This is a dermoscopic photograph of a skin lesion — 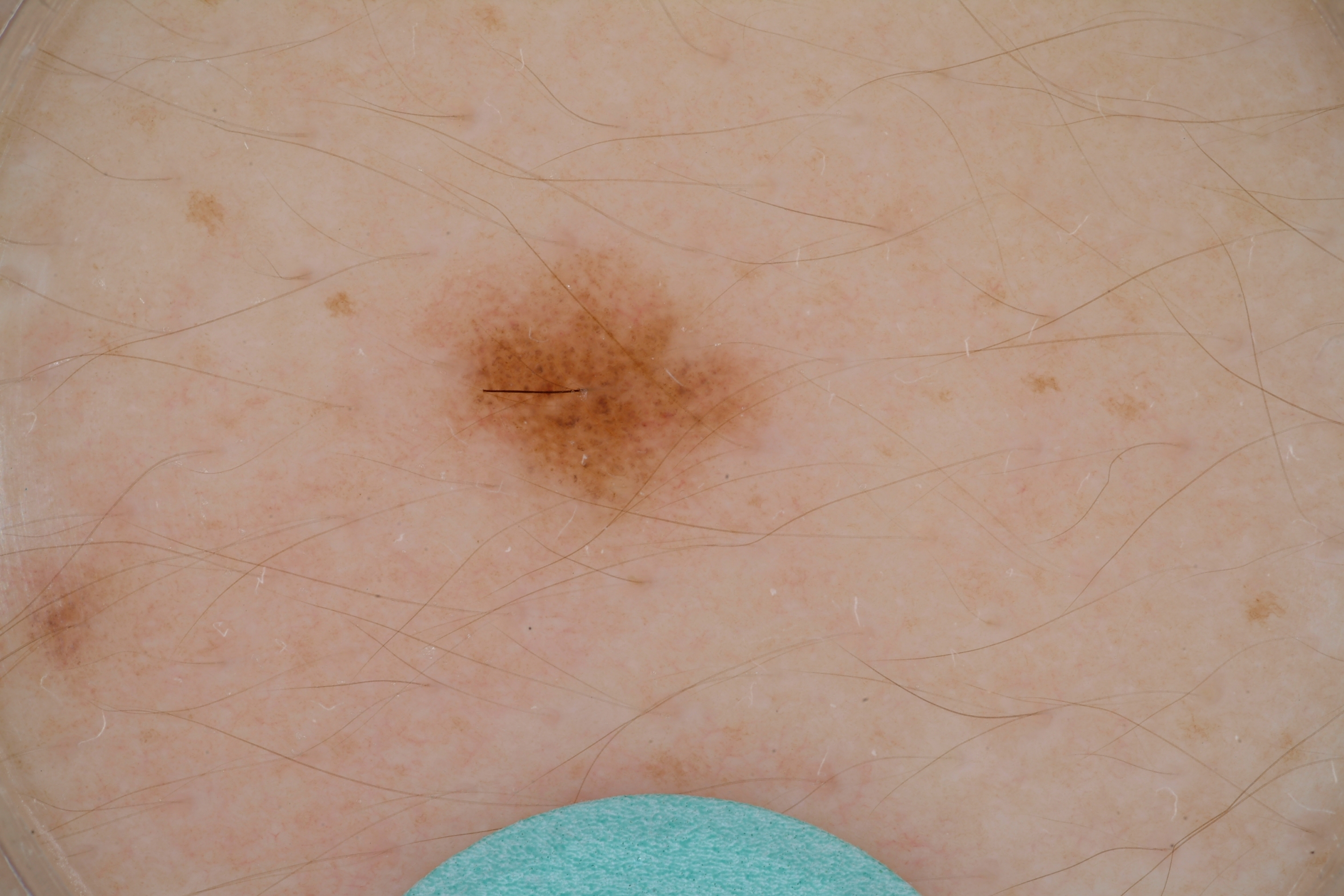Notes:
- lesion location: box(395, 225, 787, 549)
- absent dermoscopic findings: streaks and globules
- impression: a benign skin lesion